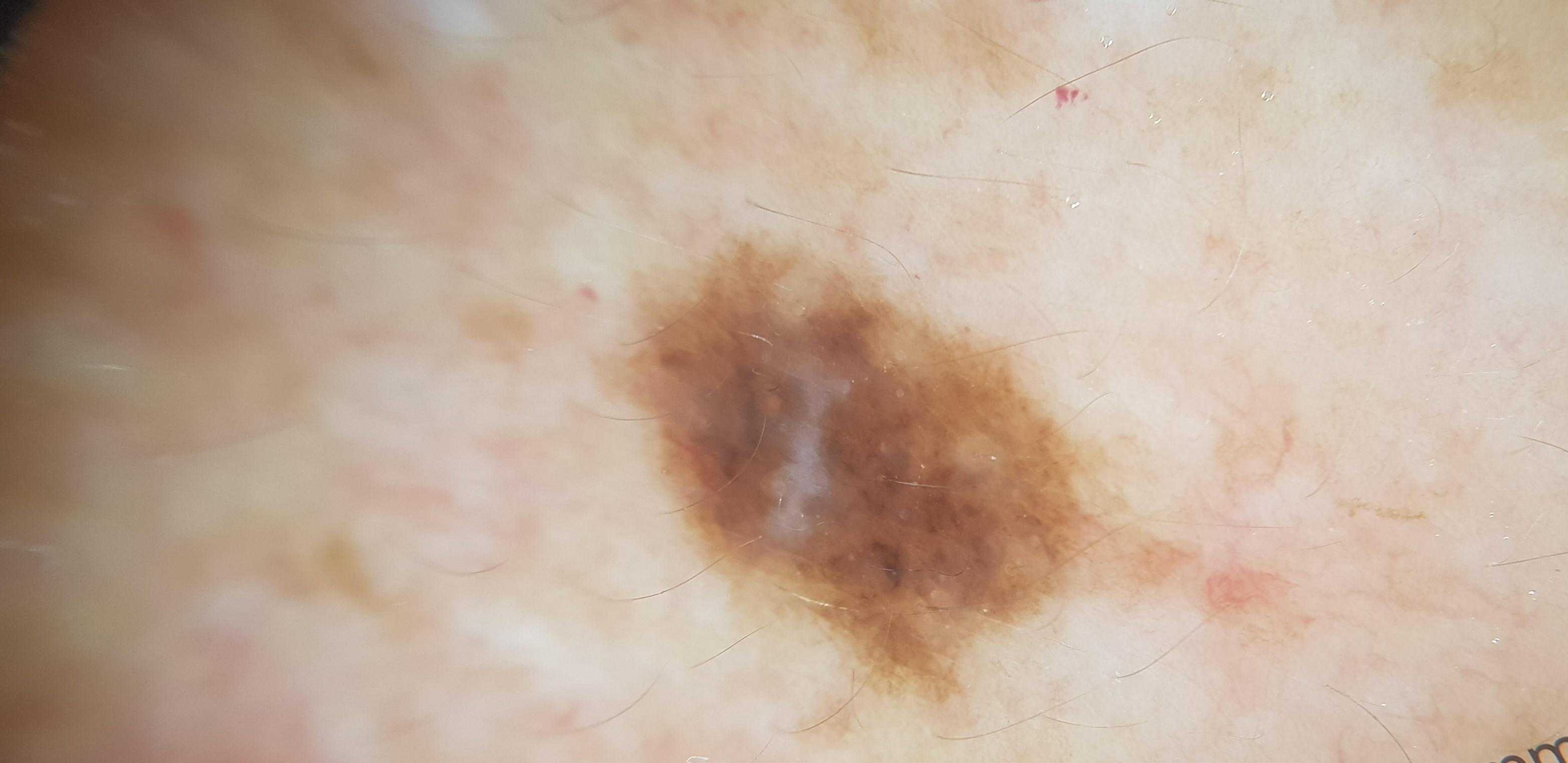Notes:
- skin phototype: II
- modality: contact-polarized dermoscopy
- patient: female, approximately 60 years of age
- body site: the trunk (the posterior trunk)
- diagnostic label: Nevus (biopsy-proven)